A skin lesion imaged with a dermatoscope:
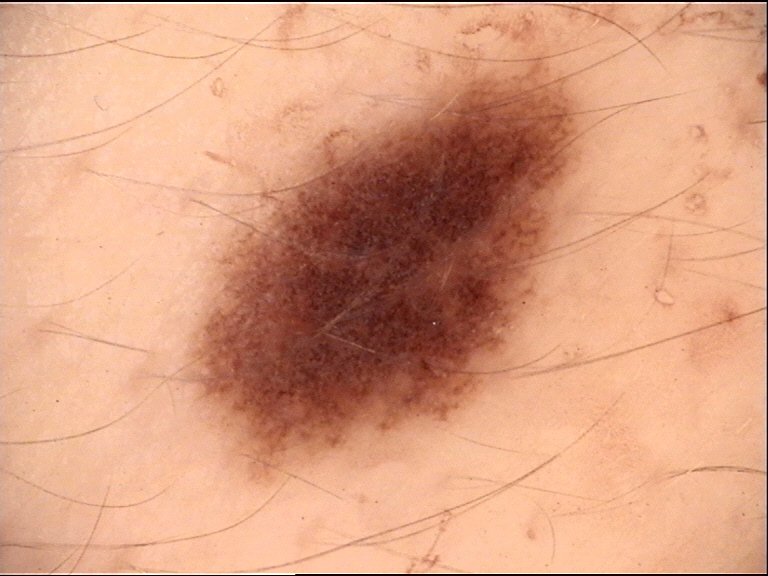The diagnosis was a dysplastic junctional nevus.